The photograph is a close-up of the affected area:
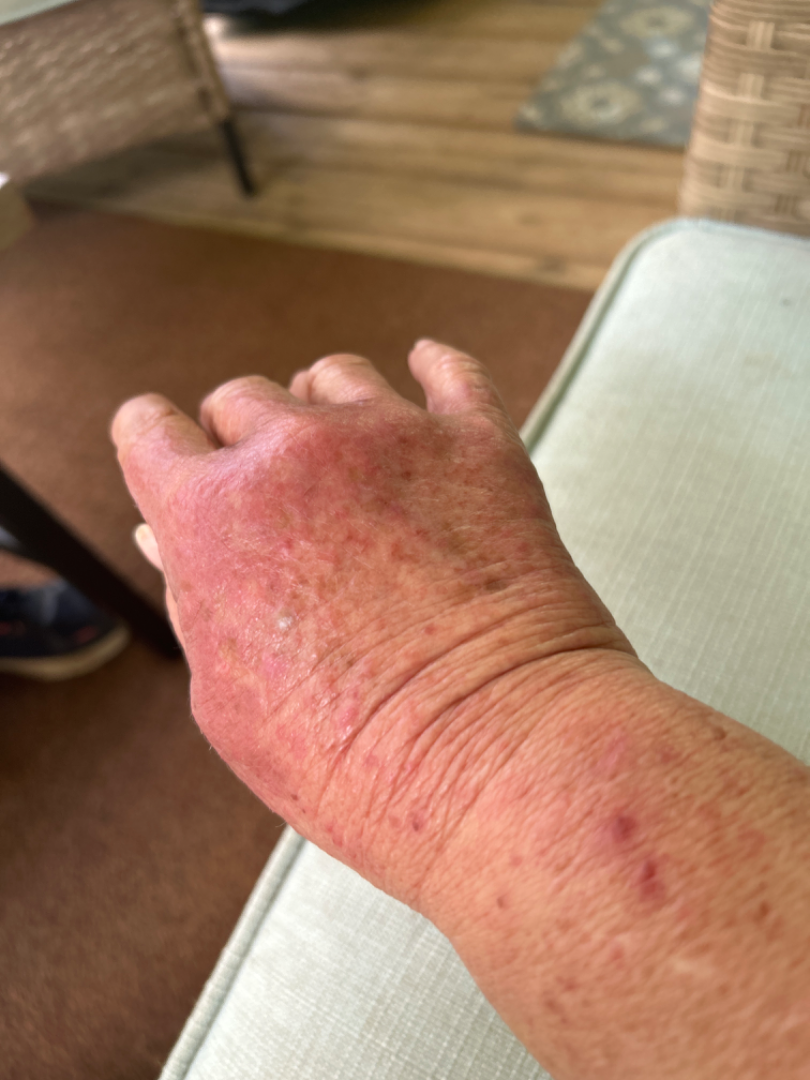Notes:
* assessment: unable to determine